The contributor is a female aged 18–29; located on the arm; a close-up photograph: 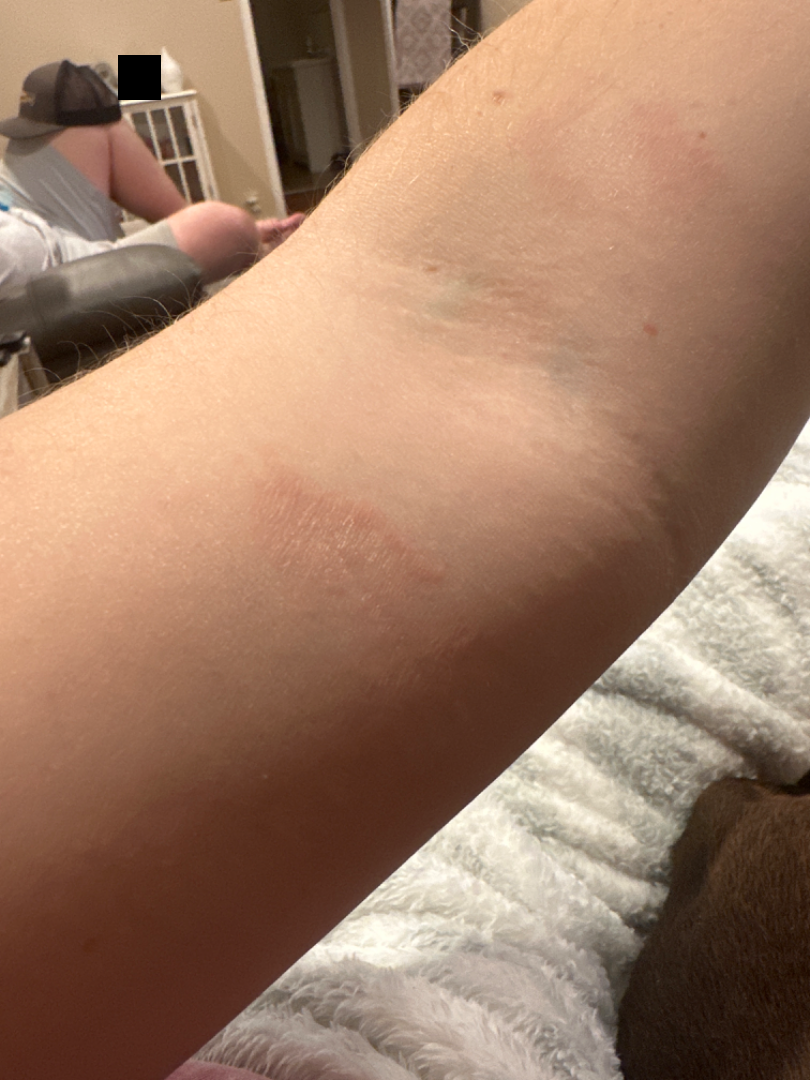Review: On photographic review: most likely Lichen planus/lichenoid eruption; also consider Parapsoriasis; also raised was Eczema.